A dermoscopy image of a single skin lesion:
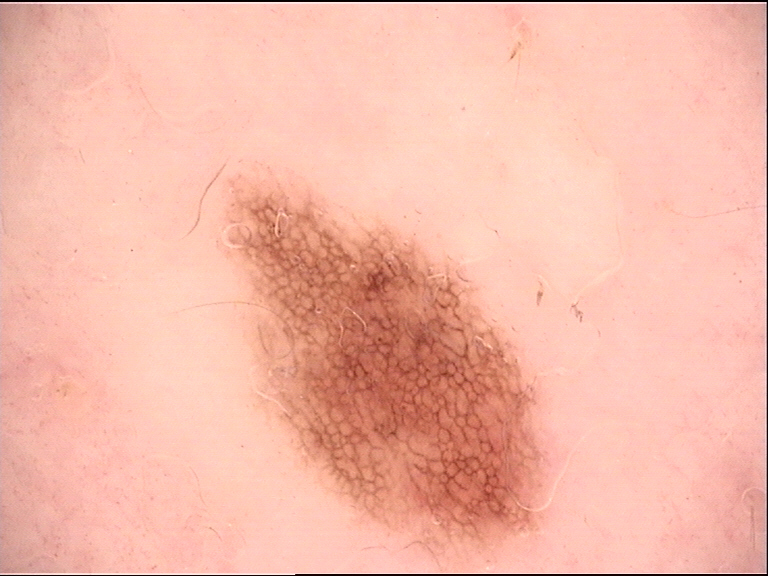class: dysplastic junctional nevus (expert consensus).